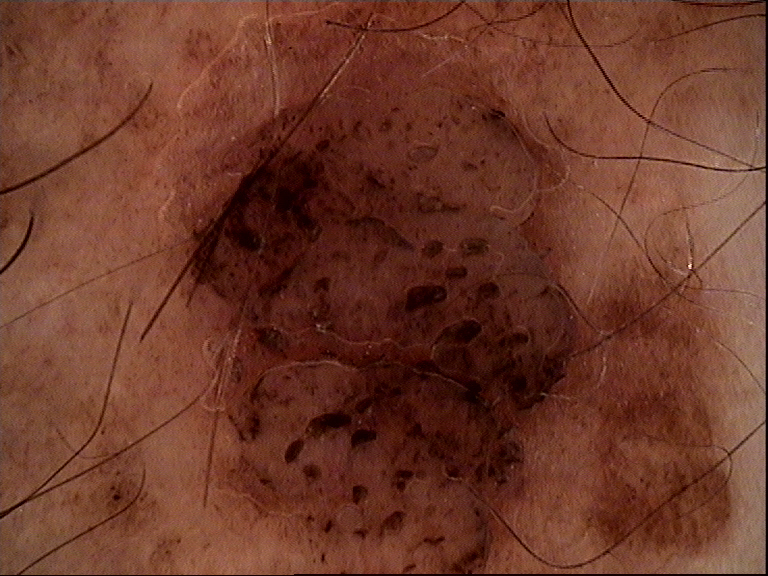A dermoscopic close-up of a skin lesion.
Labeled as a banal lesion — a congenital compound nevus.